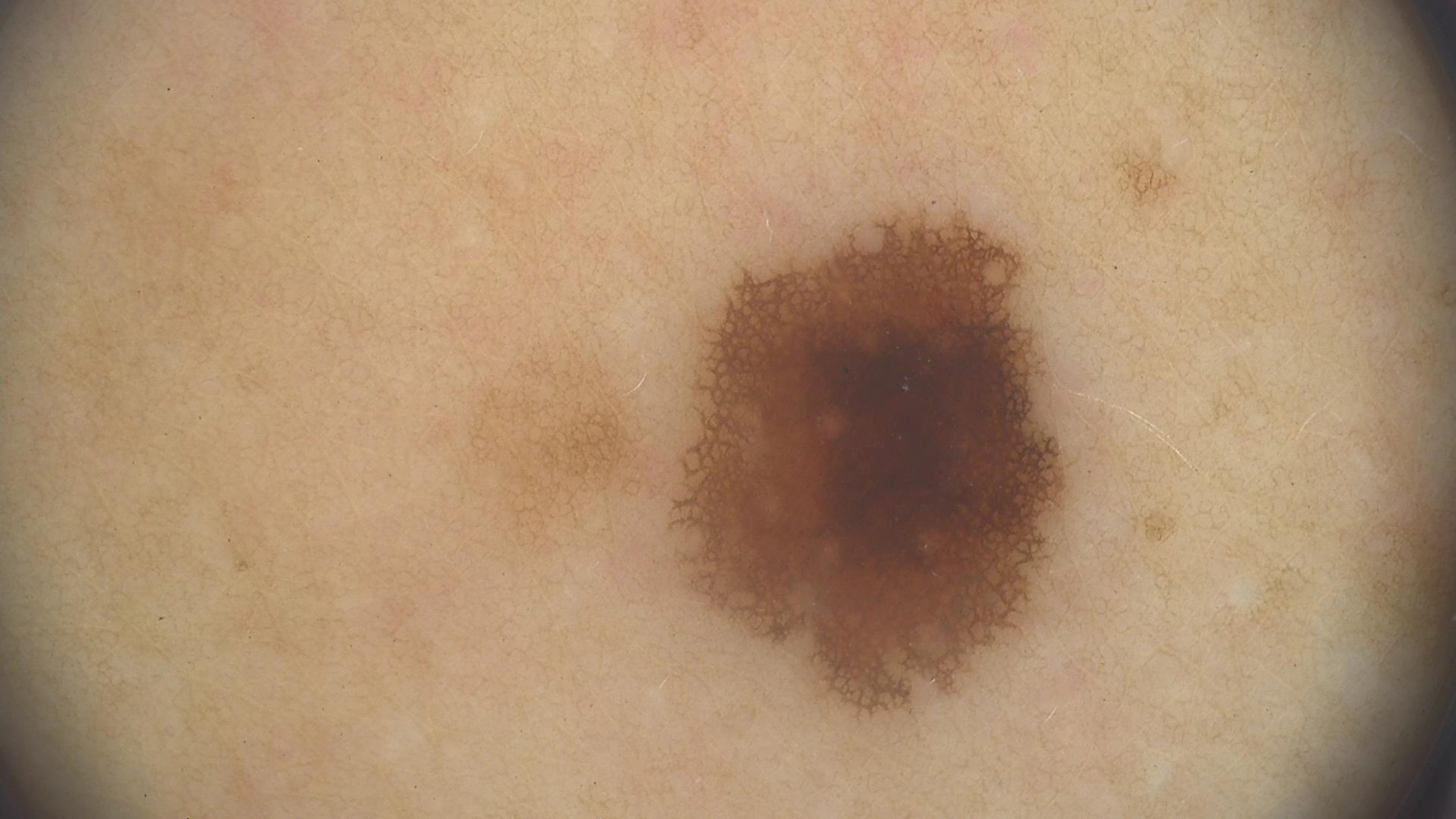Case: Dermoscopy of a skin lesion. Impression: Consistent with a benign lesion — a dysplastic junctional nevus.